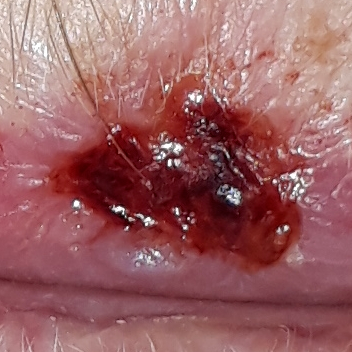{"symptoms": {"present": ["itching", "bleeding", "elevation", "pain"]}, "diagnosis": {"name": "basal cell carcinoma", "code": "BCC", "malignancy": "malignant", "confirmation": "histopathology"}}